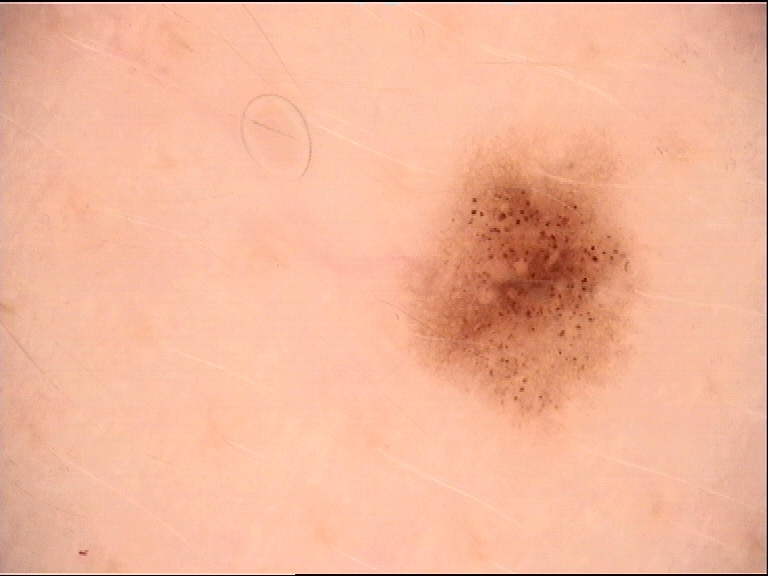The diagnosis was a dysplastic junctional nevus.